A female subject aged 58-62: 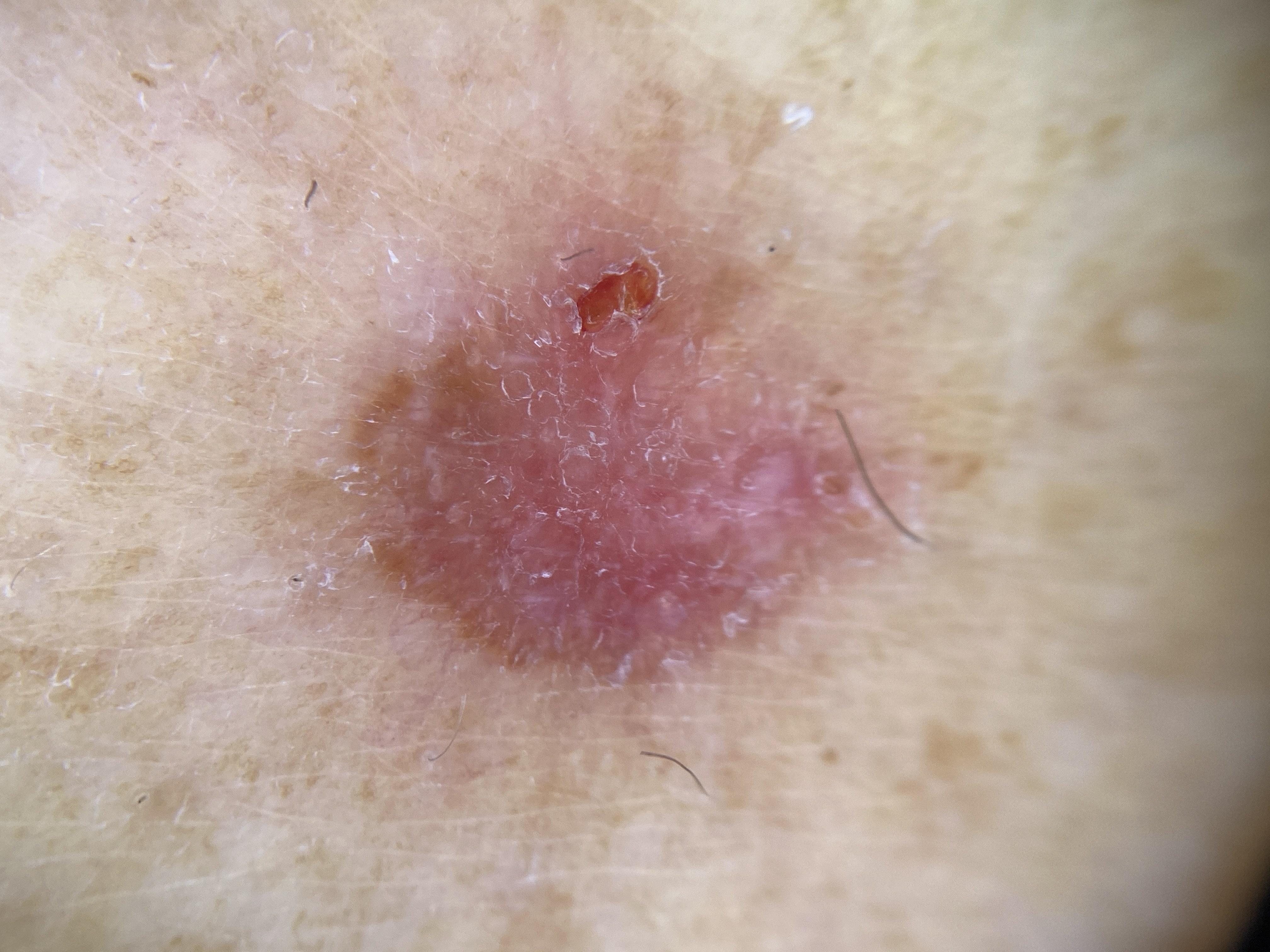On biopsy, the diagnosis was a basal cell carcinoma.